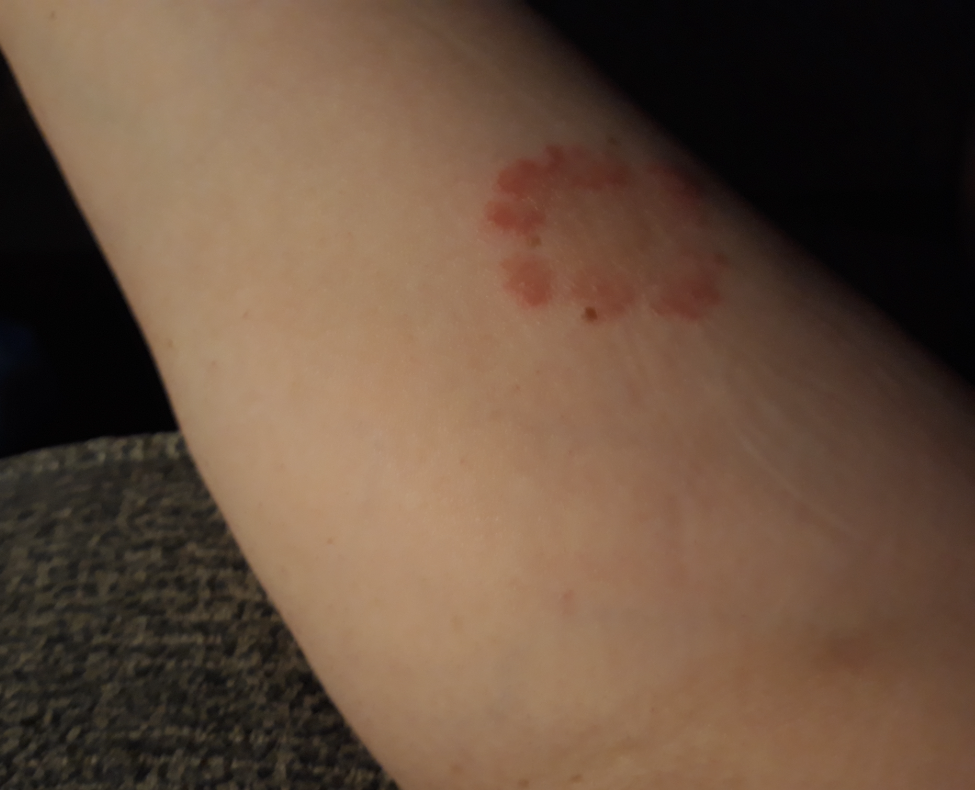Review:
The skin condition could not be confidently assessed from this image.